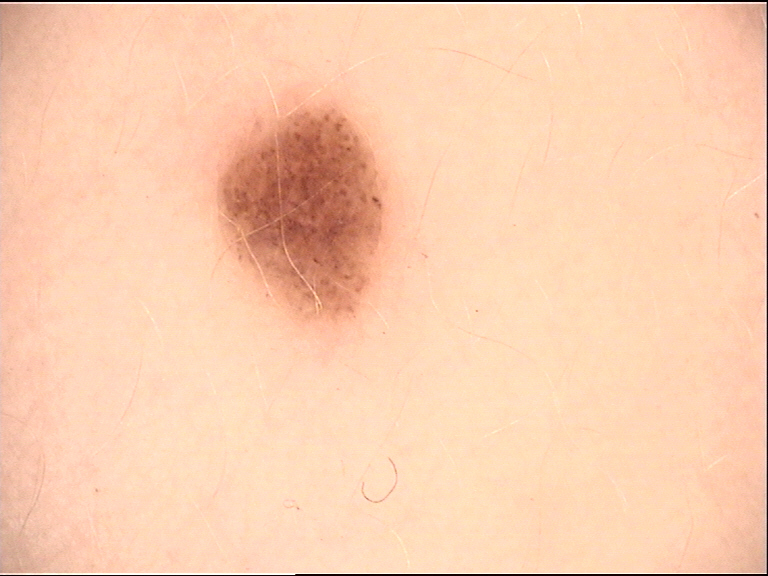A dermoscopy image of a single skin lesion. Classified as a banal lesion — a compound nevus.